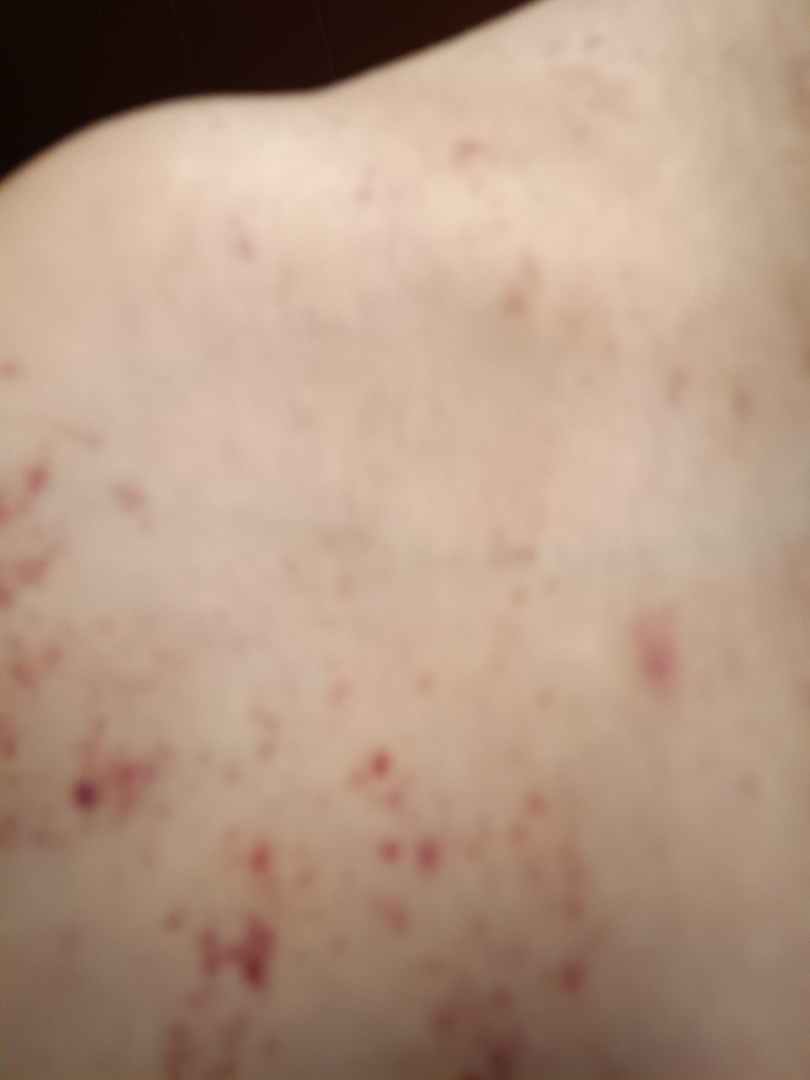Review: The reviewer was unable to grade this case for skin condition. Patient information: A close-up photograph. Fitzpatrick III.